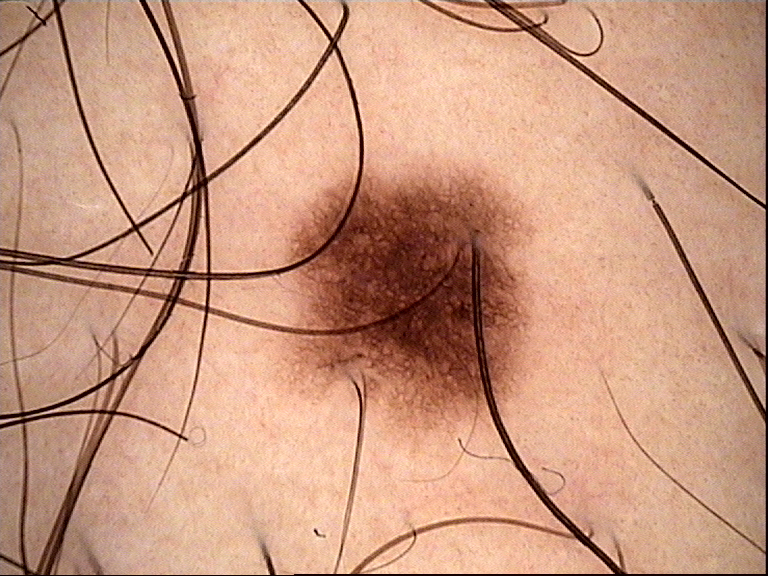Consistent with a dysplastic junctional nevus.